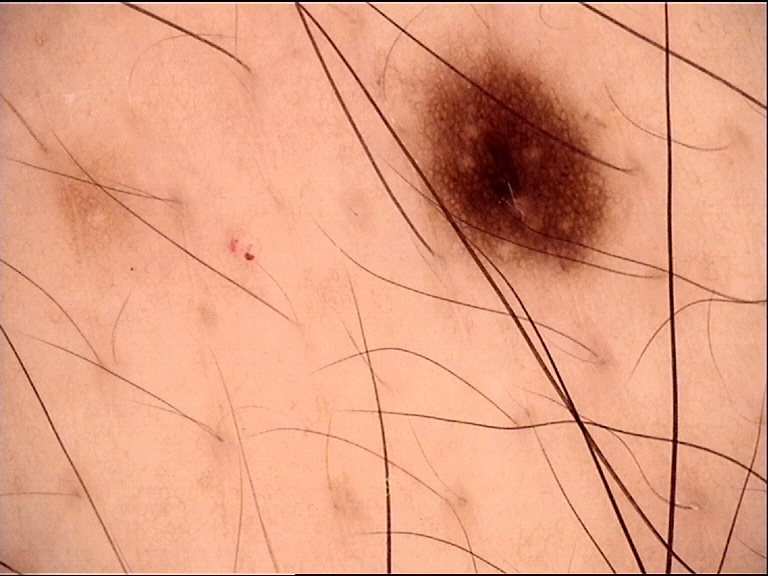The architecture is that of a banal lesion. The diagnosis was a junctional nevus.